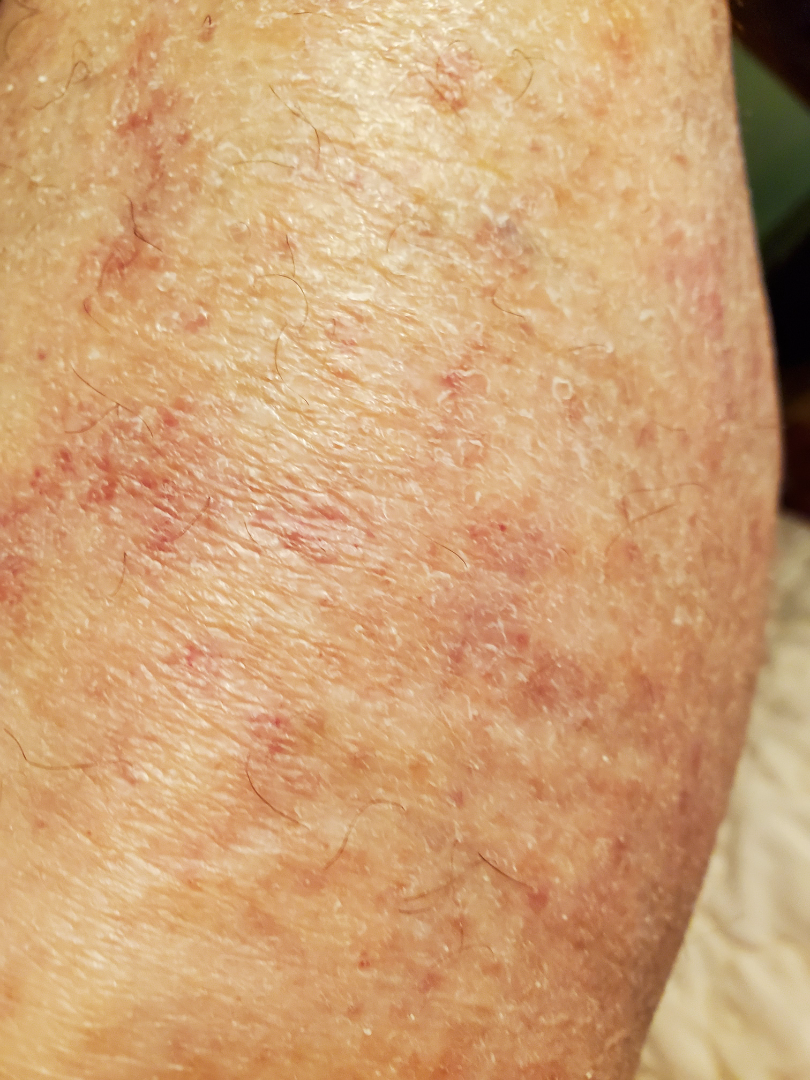History: A close-up photograph. The patient considered this a rash. The patient indicates the lesion is rough or flaky. Impression: A single dermatologist reviewed the case: most consistent with Pigmented purpuric eruption; an alternative is Stasis Dermatitis; possibly Leukocytoclastic Vasculitis.